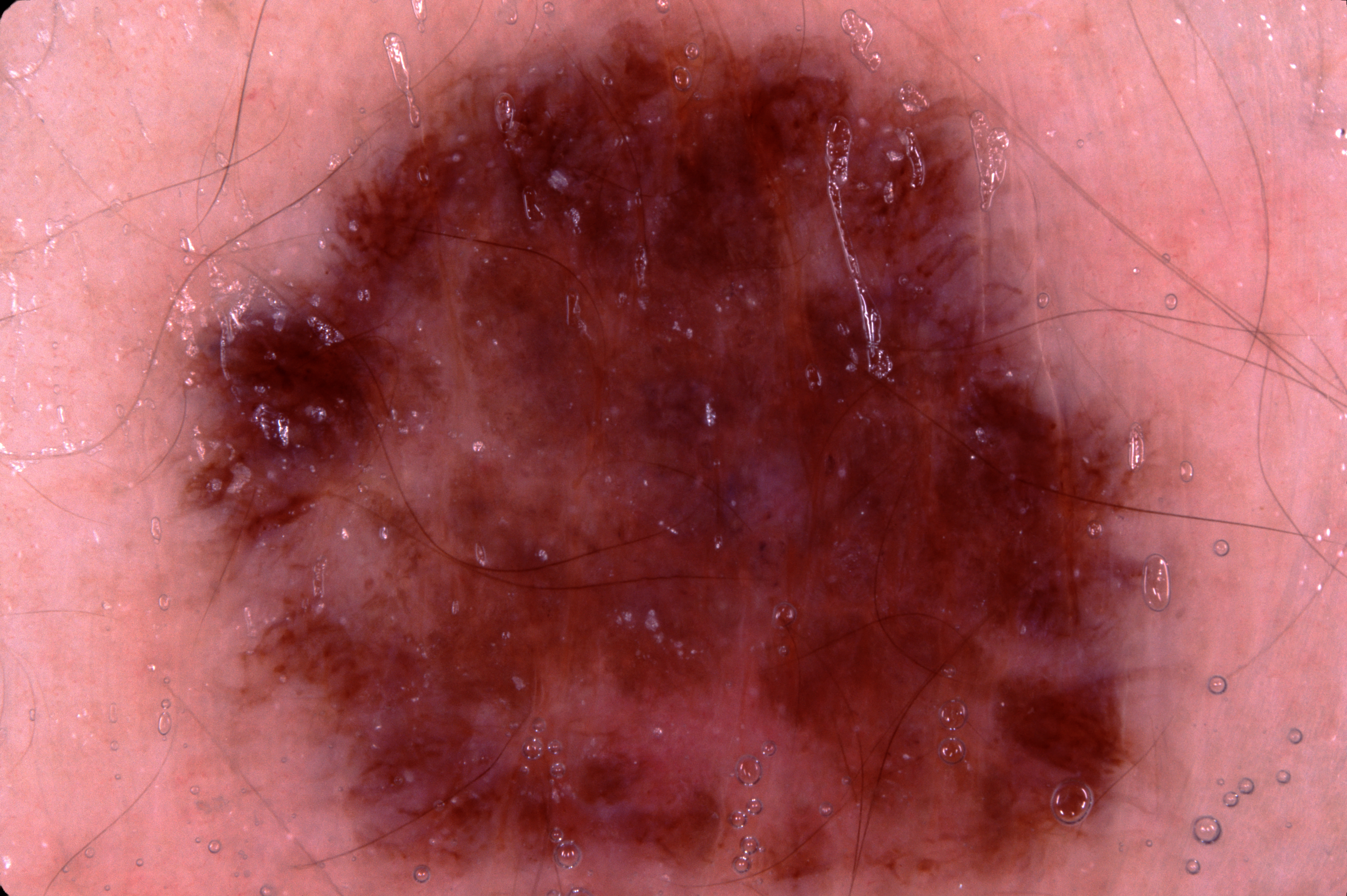The subject is a male aged 23 to 27. A dermoscopic image of a skin lesion. The lesion's extent is x1=179, y1=8, x2=1240, y2=895. The dermoscopic pattern shows pigment network; no milia-like cysts, streaks, or negative network. Clinically diagnosed as a melanocytic nevus.